A male subject 65 years of age · imaged for a research study, with no referral diagnosis recorded · by self-report, a family history of skin cancer, immunosuppression, and a personal history of skin cancer: 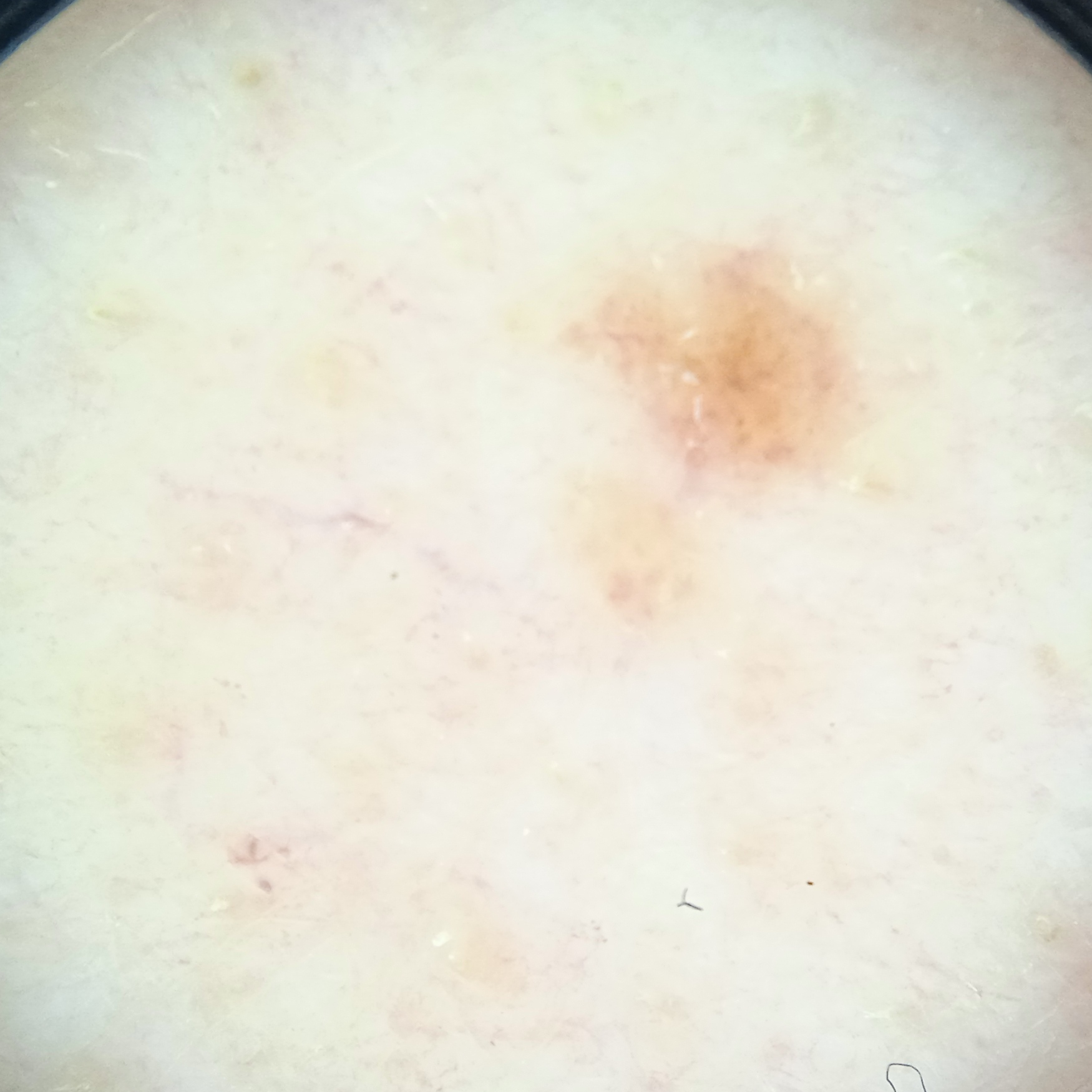The lesion is on the back. The dermatologists' assessment was a melanocytic nevus.